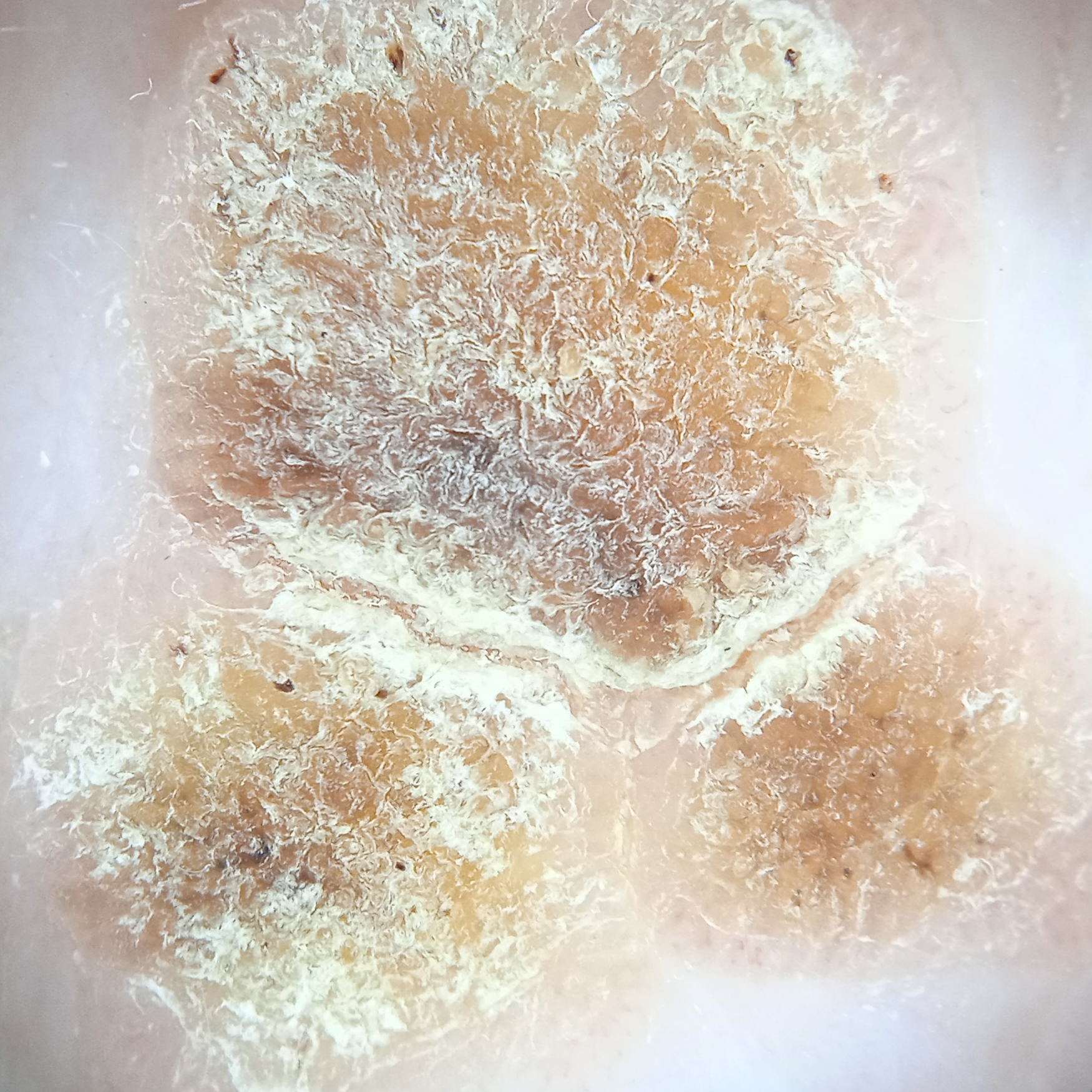relevant history = a personal history of skin cancer, a personal history of cancer; nevus count = a moderate number of melanocytic nevi; sun reaction = skin reddens with sun exposure; referral context = research study (no referral diagnosis); diameter = 14.2 mm; diagnostic label = seborrheic keratosis (dermatologist consensus).